Recorded as FST II · a smartphone photograph of a skin lesion · a female subject in their early 50s · the chart notes prior skin cancer (patient or family).
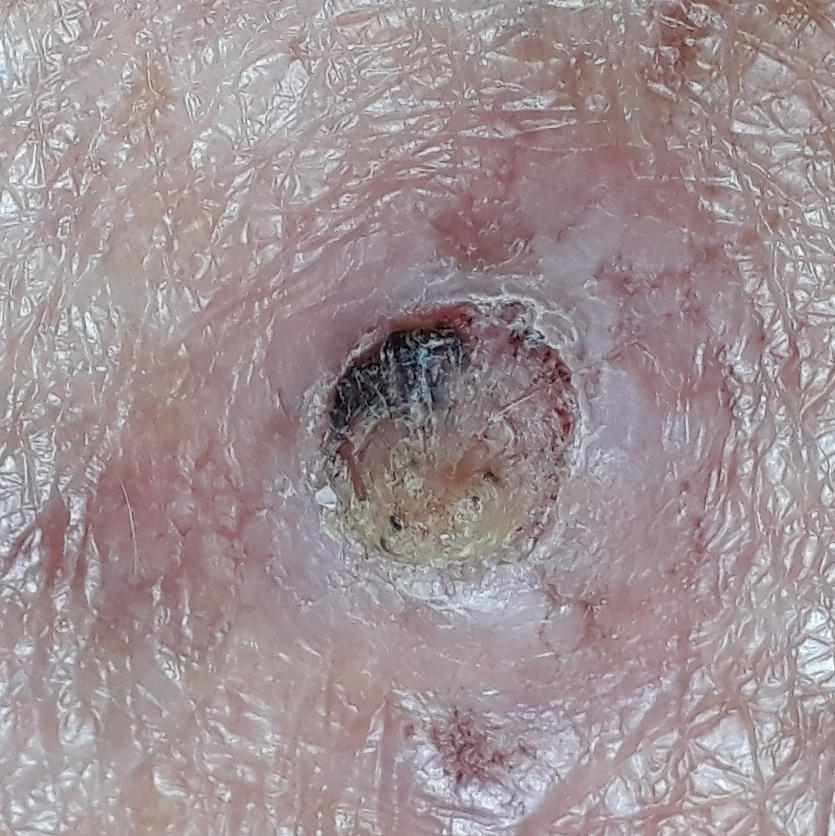Findings:
– diameter · 15x12 mm
– patient-reported symptoms · elevation, pain, itching
– diagnostic label · actinic keratosis (biopsy-proven)